An image taken at an angle, located on the arm.
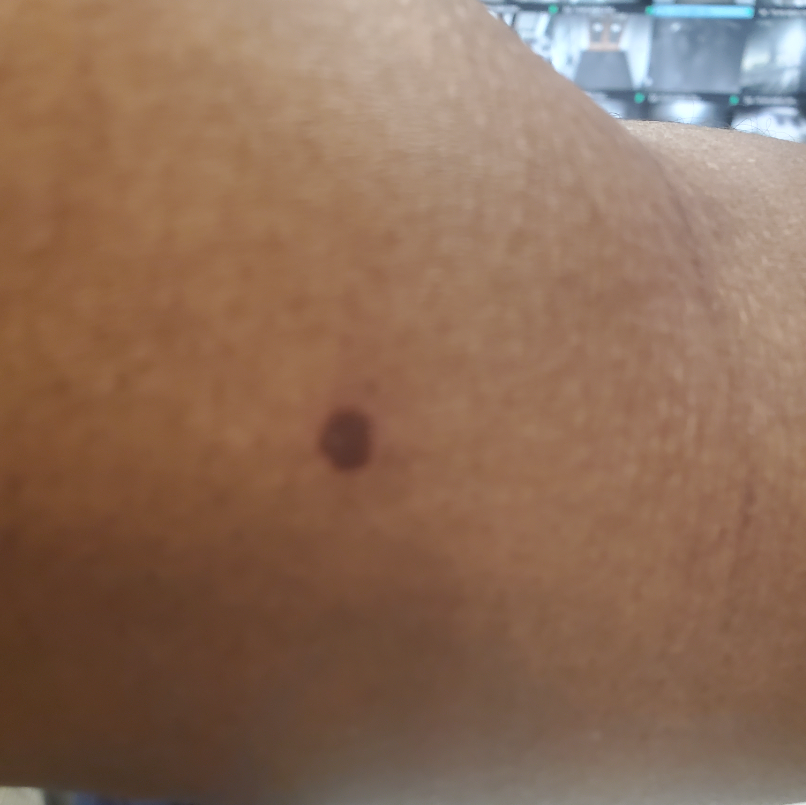Impression:
Diagnostic features were not clearly distinguishable in this photograph.
History:
The lesion is associated with darkening. FST V; lay graders estimated MST 4 or 7. Texture is reported as flat. The patient considered this skin that appeared healthy to them. Present for less than one week.